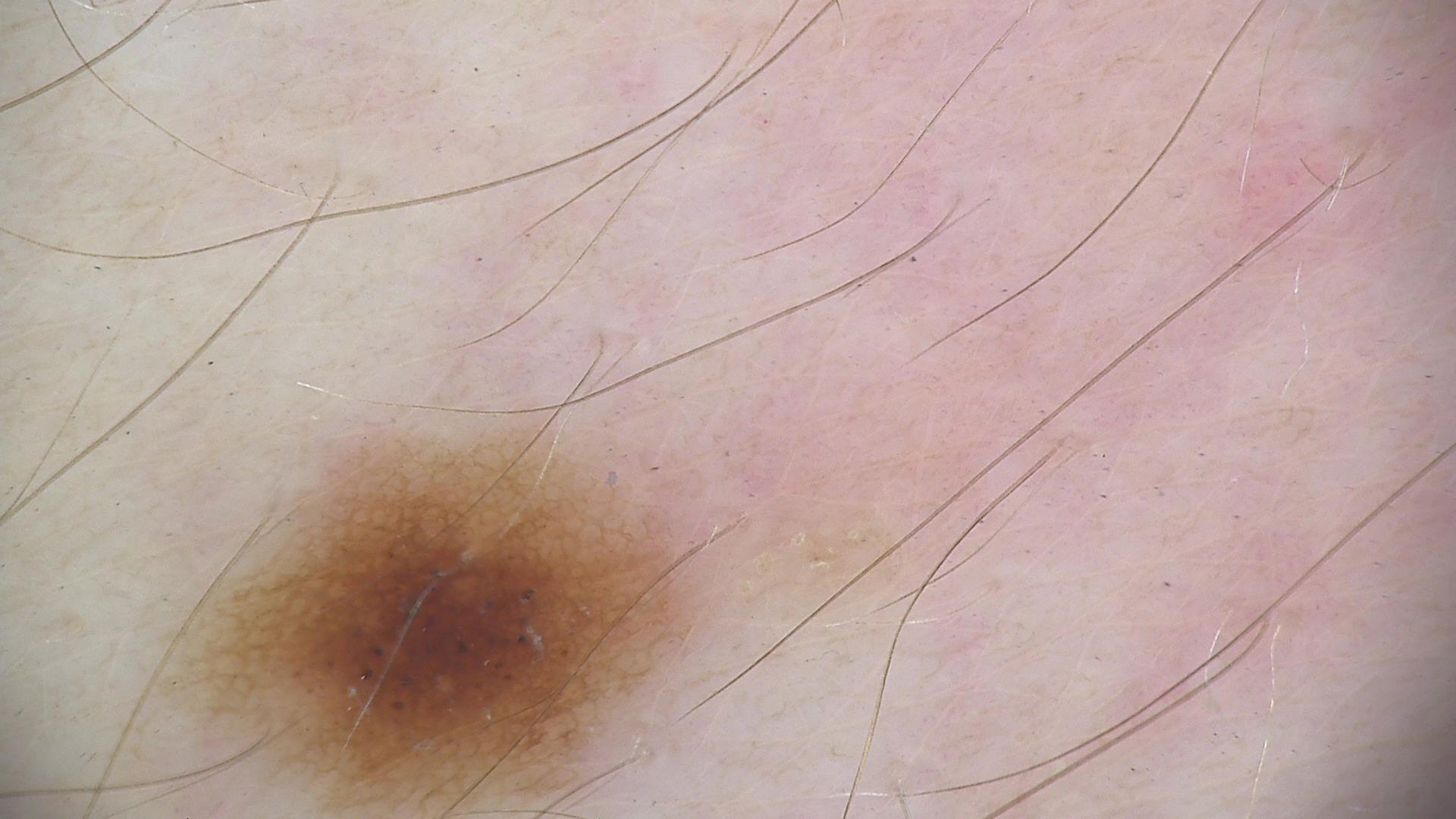Diagnosed as a dysplastic junctional nevus.